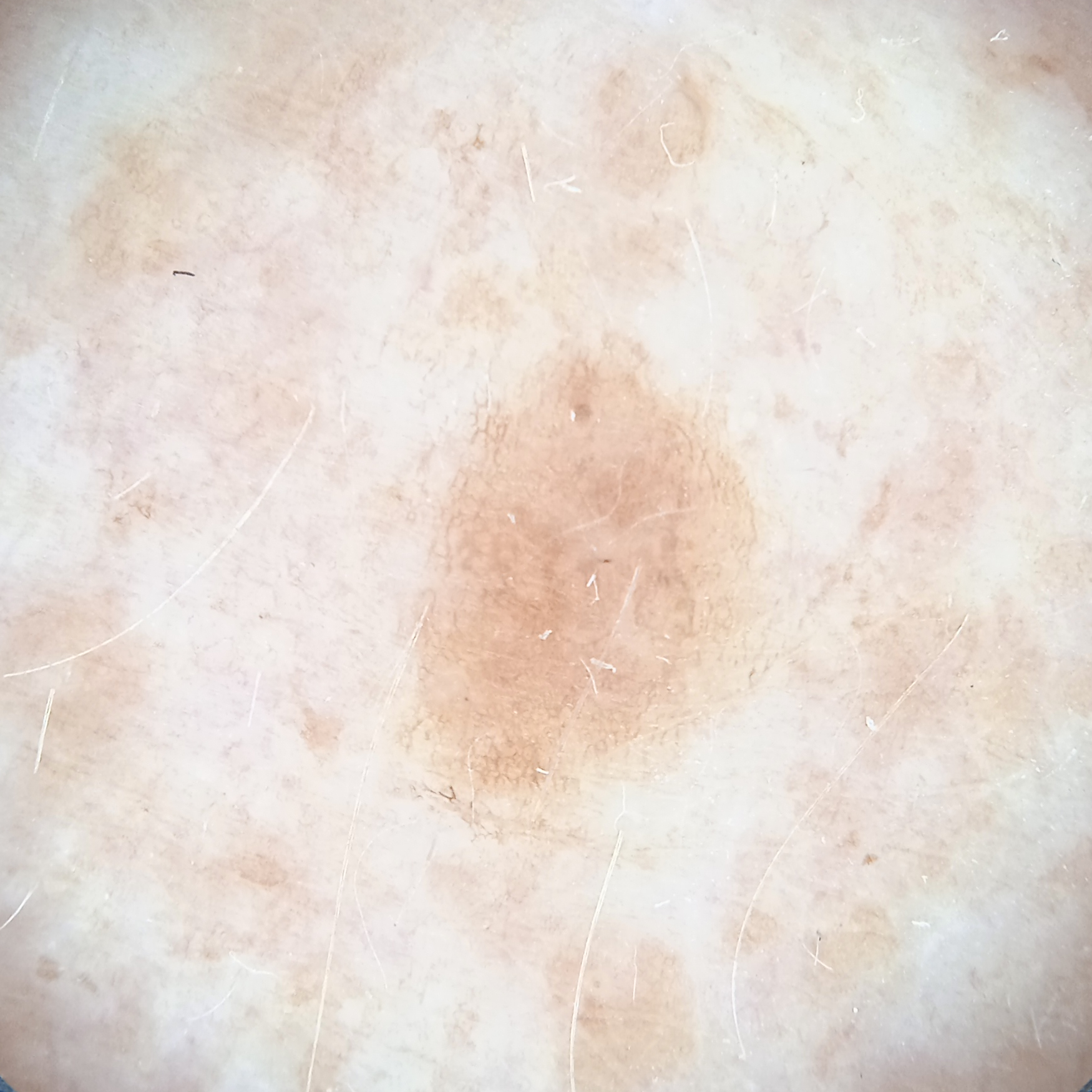On a questionnaire the patient reported no personal history of cancer and no immunosuppression. A skin lesion imaged with a dermatoscope. A female subject aged 78. Numerous moles by the patient's own estimate. Acquired for a research image collection, with no referral diagnosis. The lesion is located on an arm. The lesion measures approximately 5.3 mm. The dermatologists' assessment was a seborrheic keratosis.